The photo was captured at an angle, the affected area is the back of the hand, skin tone: Fitzpatrick skin type V:
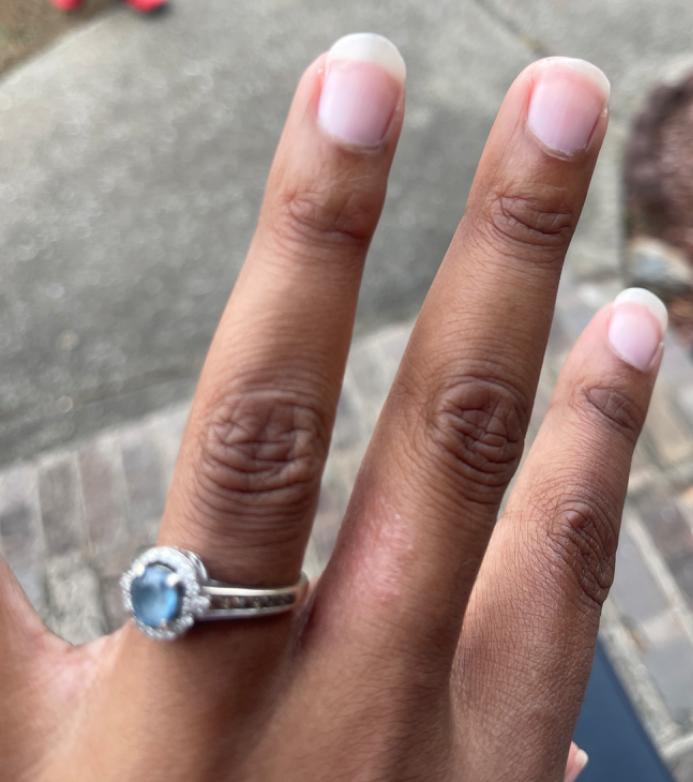Review:
The case was difficult to assess from the available photograph.